The photo was captured at an angle · the subject is 60–69, female · the lesion involves the head or neck.
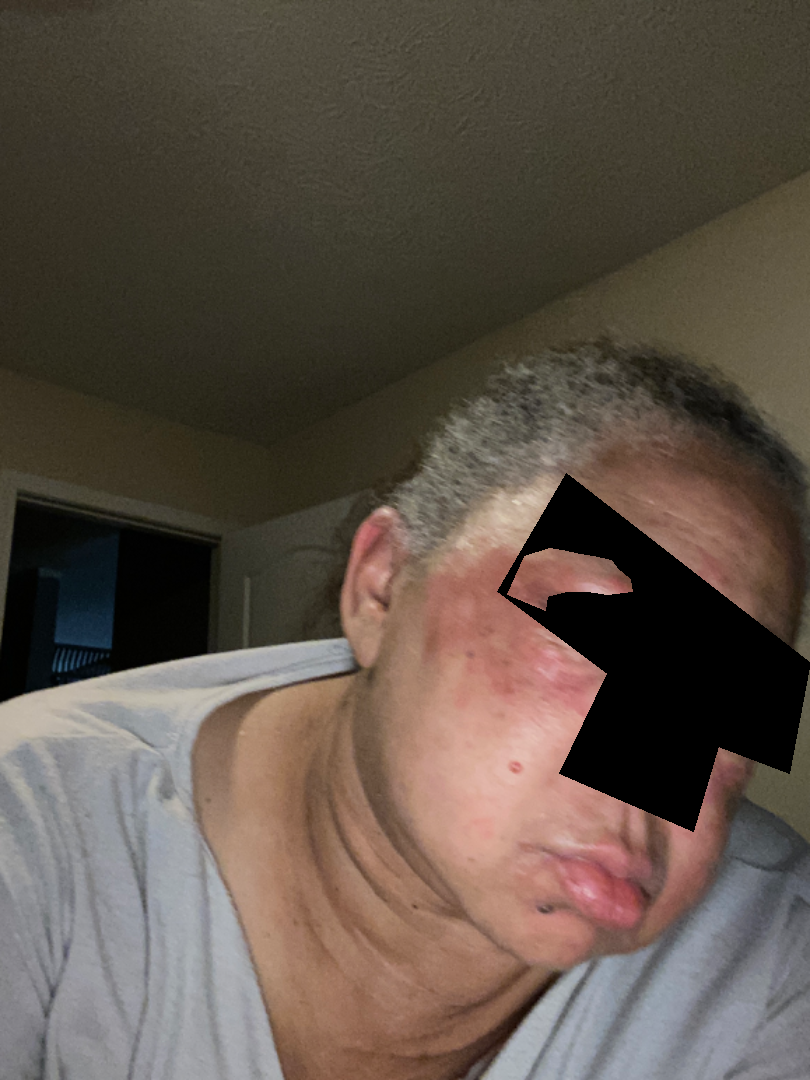On remote dermatologist review: Seborrheic Dermatitis and Eczema were each considered, in no particular order; less probable is Cutaneous lupus; lower on the differential is Allergic Contact Dermatitis; a remote consideration is Rosacea.